A skin lesion imaged with a dermatoscope: 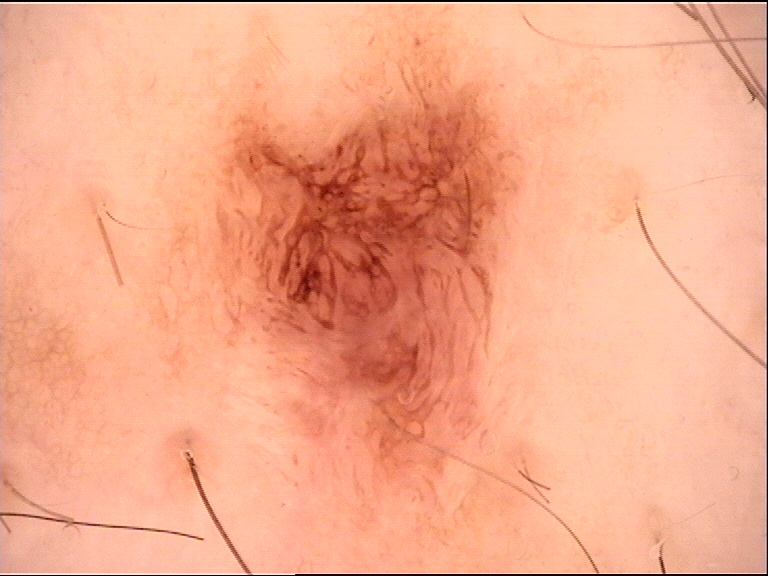Labeled as a dysplastic junctional nevus.